Dermoscopy of a skin lesion: 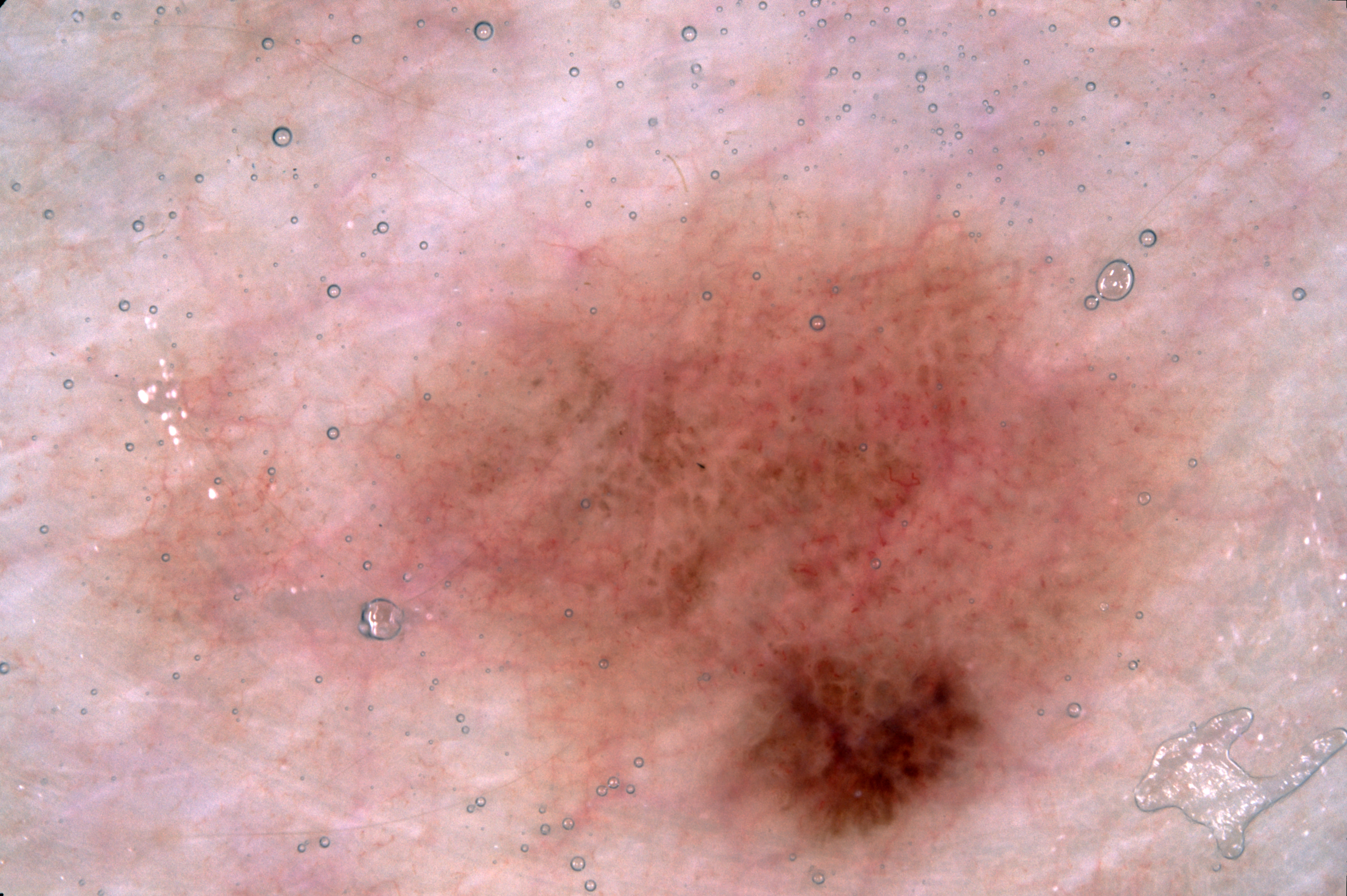As (left, top, right, bottom), the lesion is located at bbox=[100, 155, 1317, 895]. Dermoscopic assessment notes negative network and pigment network, with no streaks or milia-like cysts. The biopsy diagnosis was a melanoma, a malignant skin lesion.